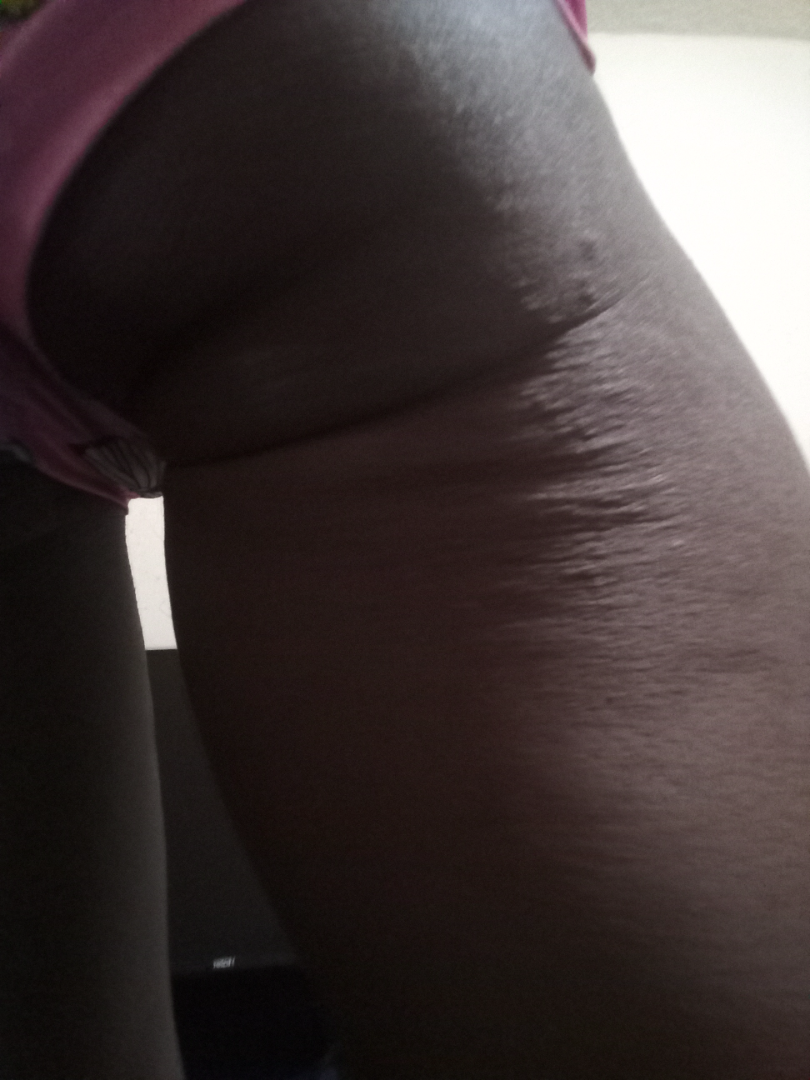The reviewing dermatologist was unable to assign a differential diagnosis from the image.
This image was taken at an angle.
The subject is female.
Texture is reported as rough or flaky, flat and raised or bumpy.
The patient indicates the condition has been present for less than one week.
Skin tone: self-reported Fitzpatrick IV.
The lesion involves the leg.